The affected area is the leg; the contributor is 40–49, female; this is a close-up image.
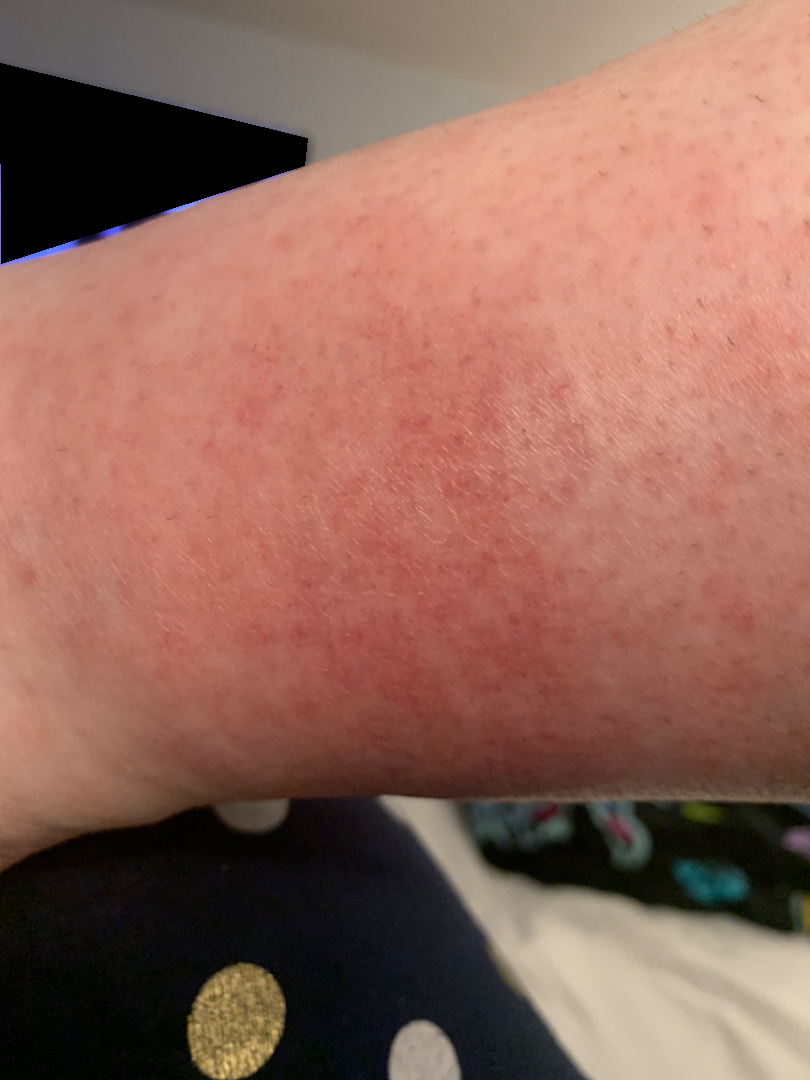The lesion is described as flat. No relevant systemic symptoms. Symptoms reported: itching and pain. Skin tone: lay graders estimated Monk skin tone scale 2. The contributor notes the condition has been present for less than one week. The patient considered this a rash. Most consistent with Stasis Dermatitis.